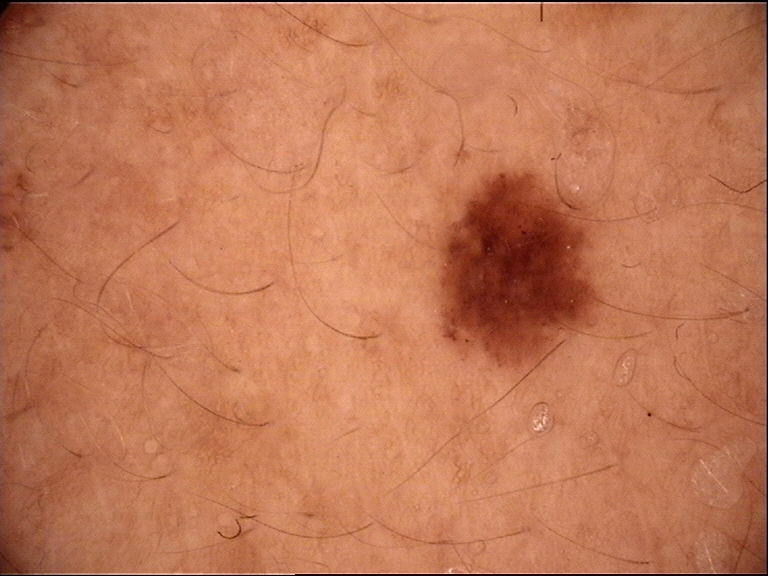image: dermoscopy | class: dysplastic junctional nevus (expert consensus).